Fitzpatrick phototype IV; lay reviewers estimated Monk Skin Tone 3. The lesion involves the arm and leg. The subject is 18–29, female. This is a close-up image. Texture is reported as fluid-filled — 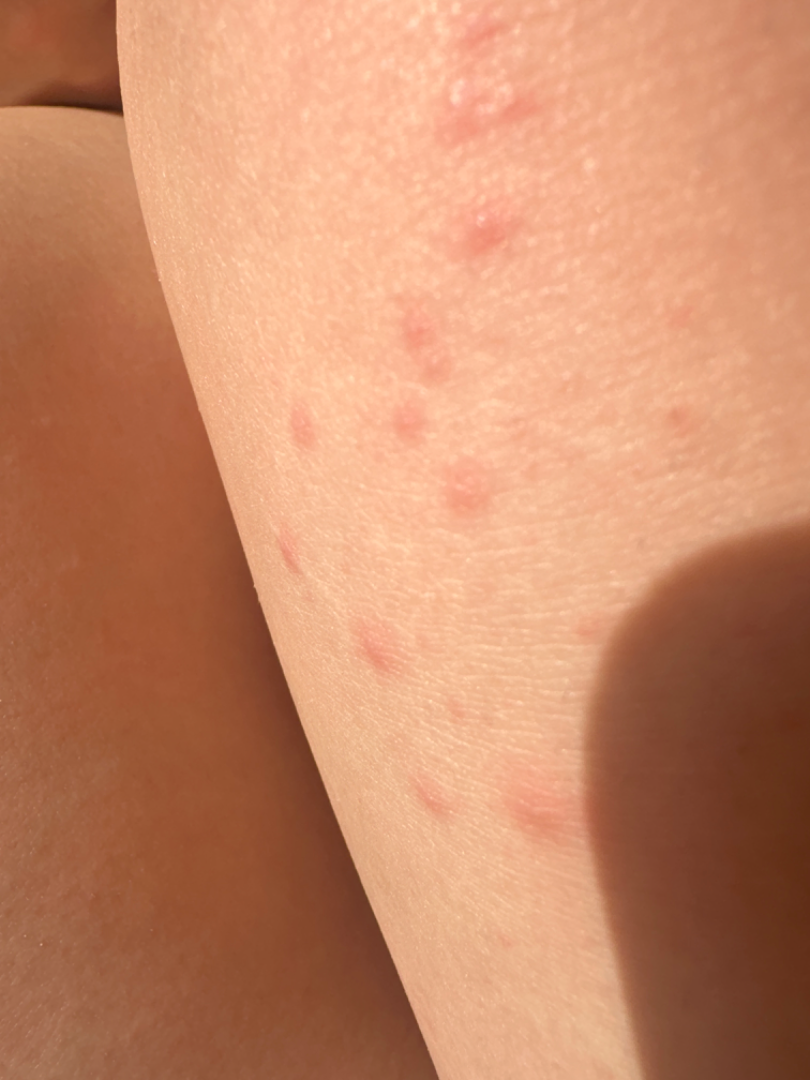On remote dermatologist review: Folliculitis (primary).